An image taken at a distance; the affected area is the front of the torso, back of the torso, leg and arm:
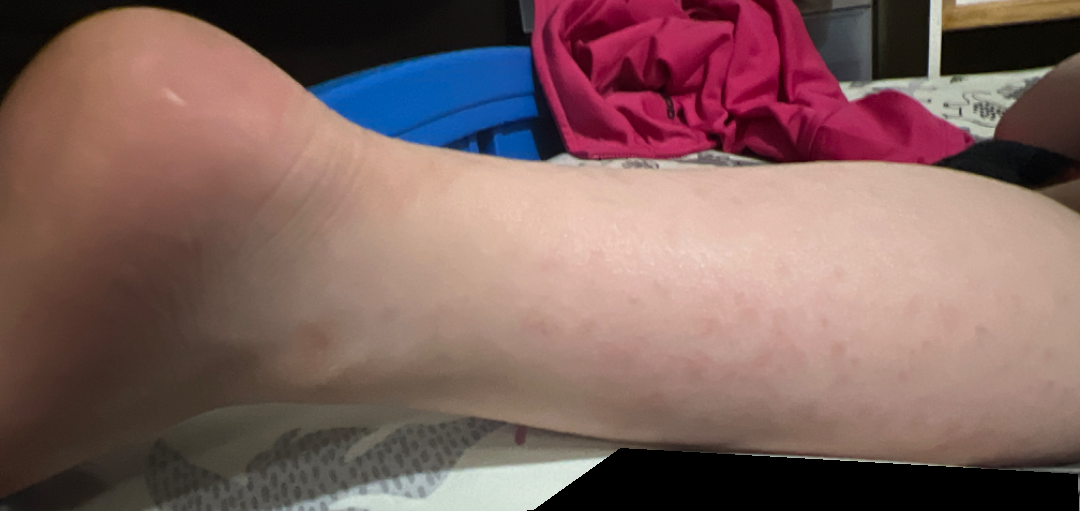Q: Fitzpatrick or Monk tone?
A: FST II; non-clinician graders estimated 2 on the MST
Q: How long has this been present?
A: about one day
Q: What symptoms does the patient report?
A: itching and bothersome appearance
Q: Patient's own categorization?
A: a rash
Q: How does the lesion feel?
A: raised or bumpy
Q: Constitutional symptoms?
A: none reported
Q: What is the differential diagnosis?
A: the primary impression is Viral Exanthem; an alternative is Drug Rash